Reported duration is less than one week. Symptoms reported: bothersome appearance and itching. The subject is 30–39, female. The front of the torso and head or neck are involved. The patient described the issue as a rash. A close-up photograph. The lesion is described as raised or bumpy — 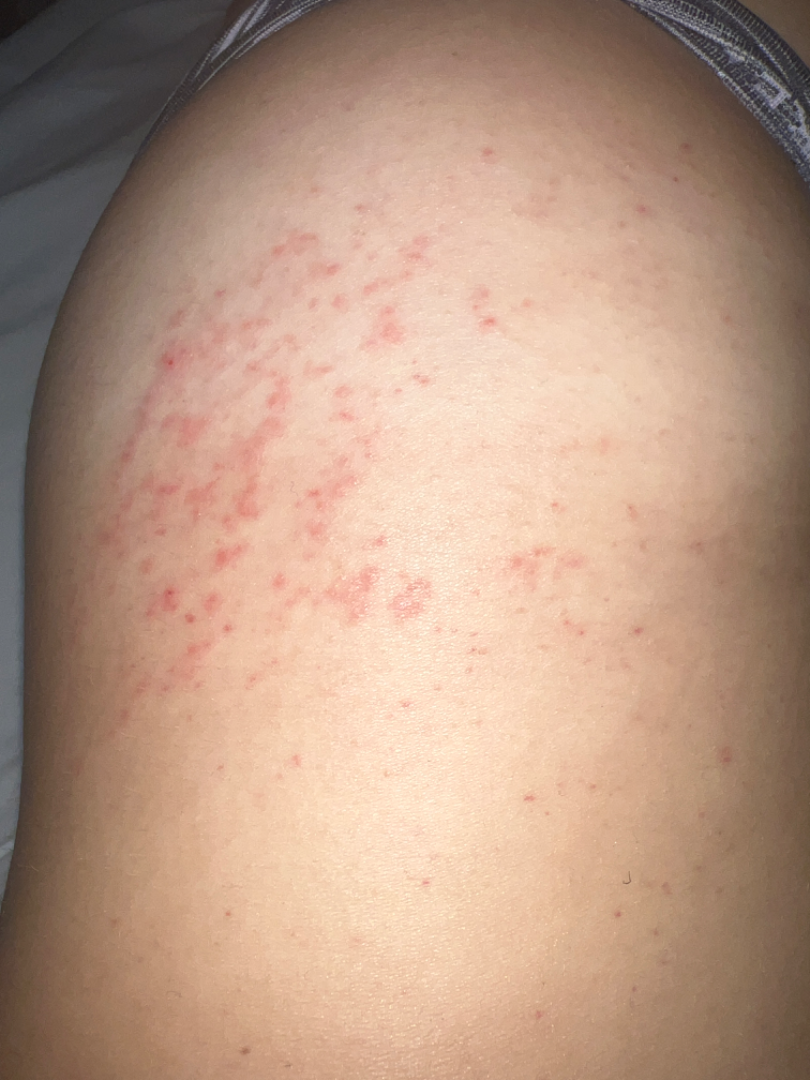Impression:
The reviewing clinician's impression was: most likely Allergic Contact Dermatitis; possibly Eczema; also consider Leukocytoclastic Vasculitis.